Dermoscopy of a skin lesion.
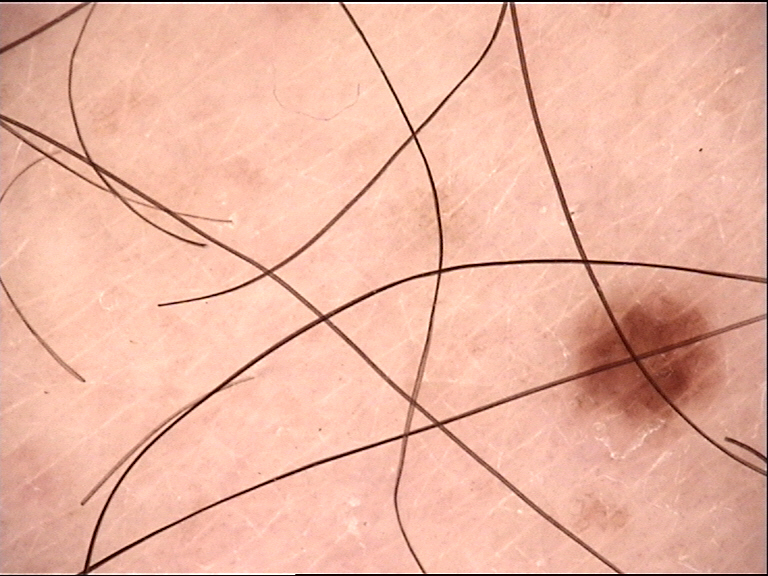Labeled as a benign lesion — a dysplastic junctional nevus.